A close-up photograph: 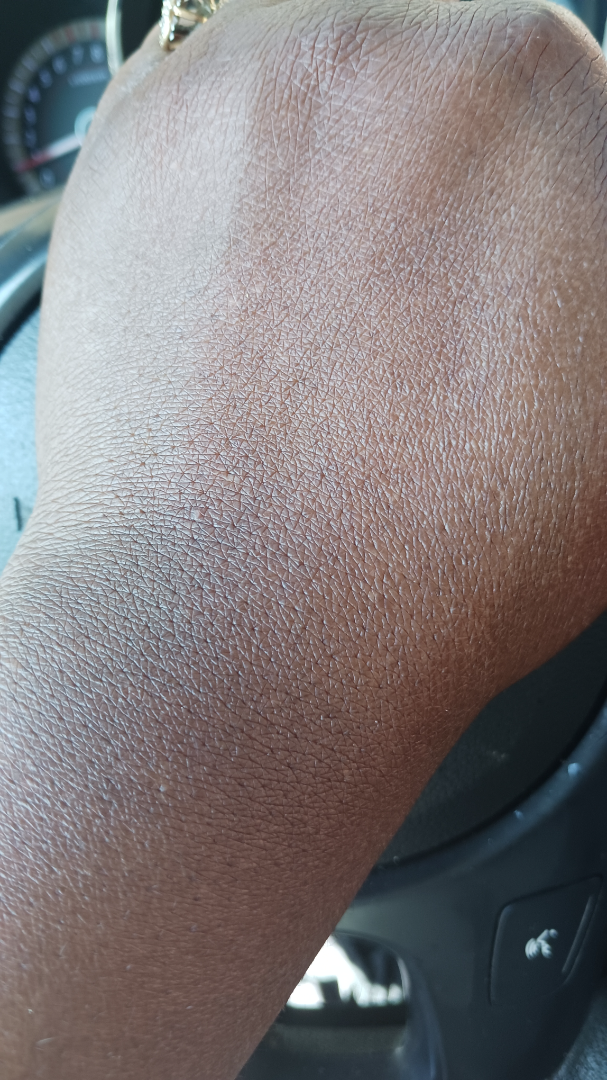differential: Drug Rash